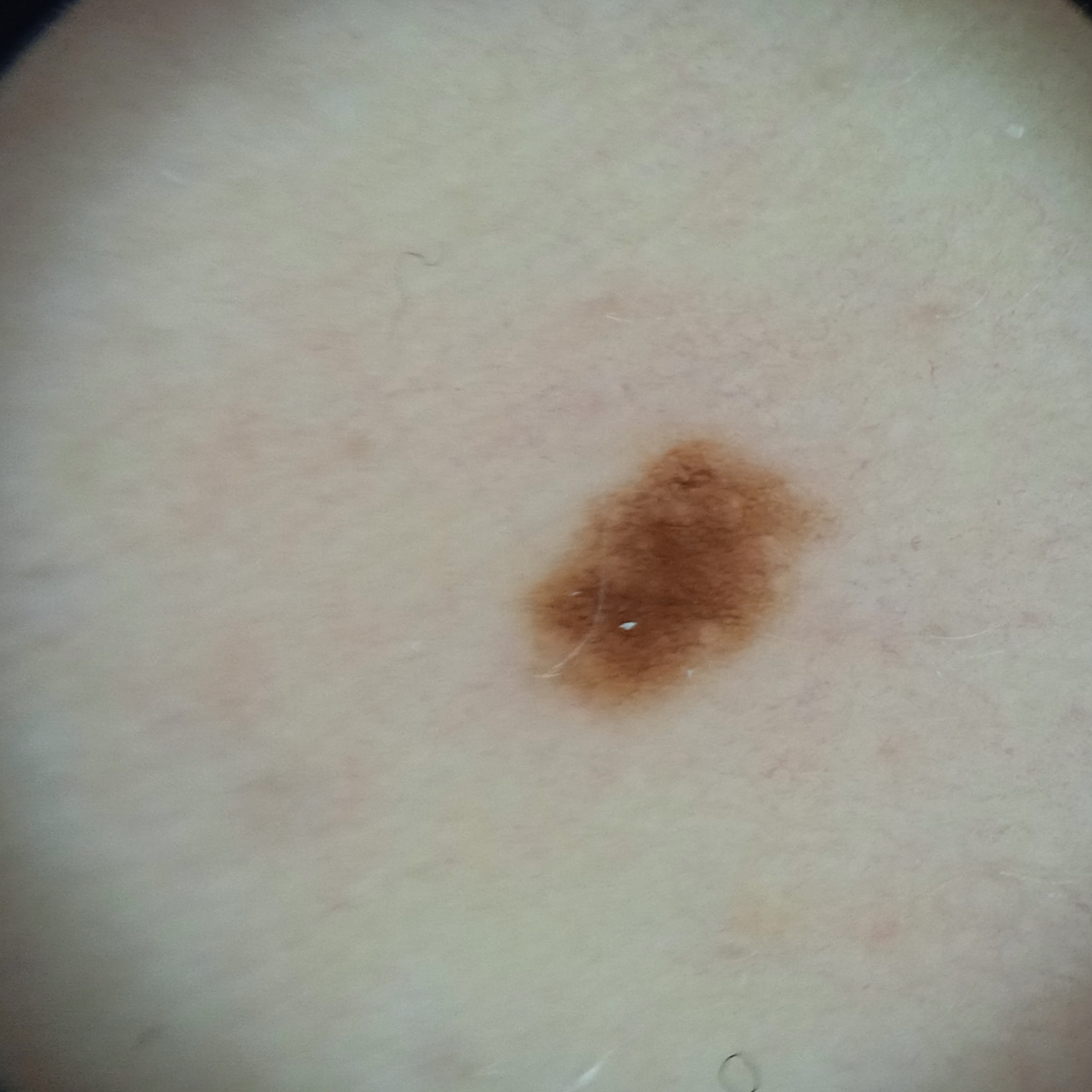• nevus count: few melanocytic nevi overall
• patient: female, aged 48
• sun reaction: skin reddens painfully with sun exposure
• relevant history: a family history of skin cancer, a history of sunbed use
• imaging: dermatoscopic image
• size: 4.3 mm
• diagnostic label: melanocytic nevus (dermatologist consensus)